A patient in their 60s — 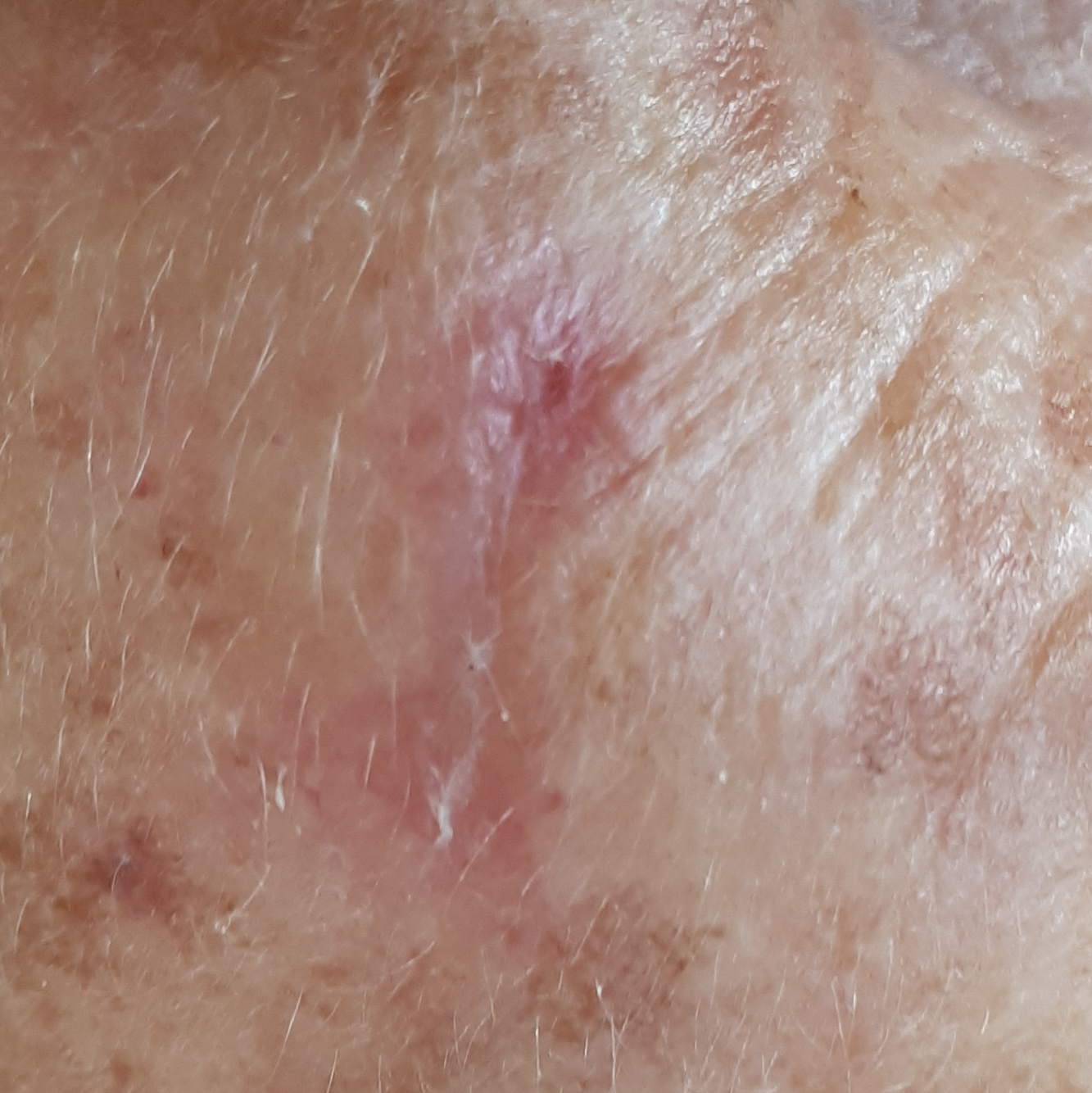Patient and lesion:
The lesion is on the face. The patient describes that the lesion has grown, but does not hurt and does not itch.
Conclusion:
Diagnosed by dermatologist consensus as an actinic keratosis.